Contact-polarized dermoscopy of a skin lesion · per the chart, melanoma in a first-degree relative: 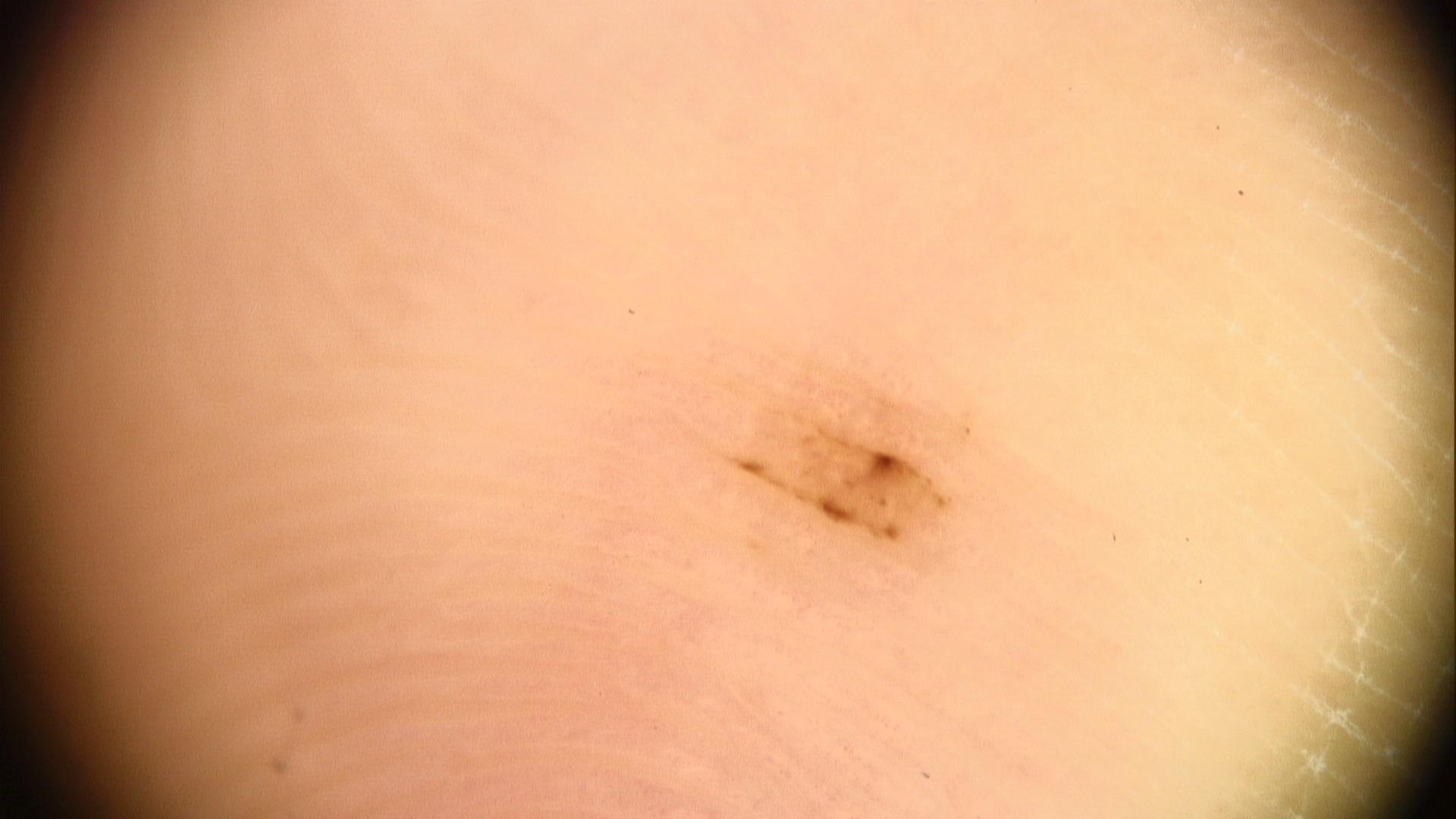Summary:
Located on a lower extremity.
Impression:
Expert review favored a benign lesion — a nevus.